The leg is involved; a close-up photograph — 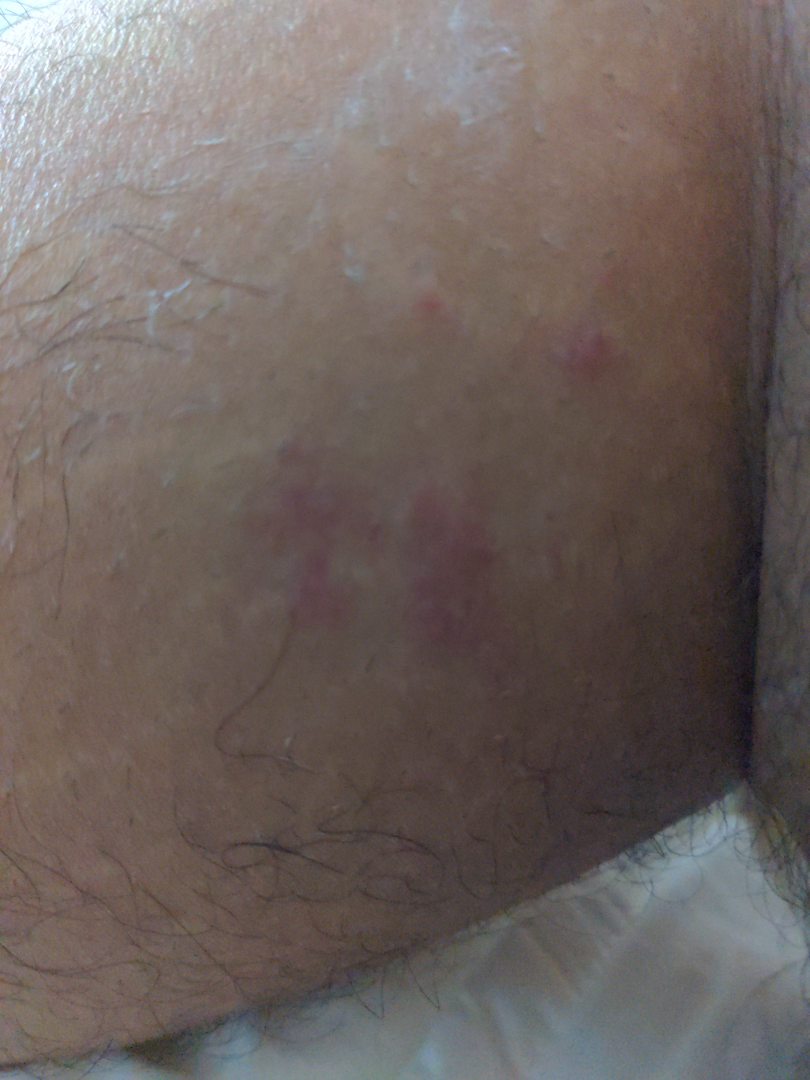assessment: not assessable | history: about one day | associated systemic symptoms: none reported | lesion symptoms: bothersome appearance, itching and darkening | patient describes the issue as: a rash | described texture: raised or bumpy.